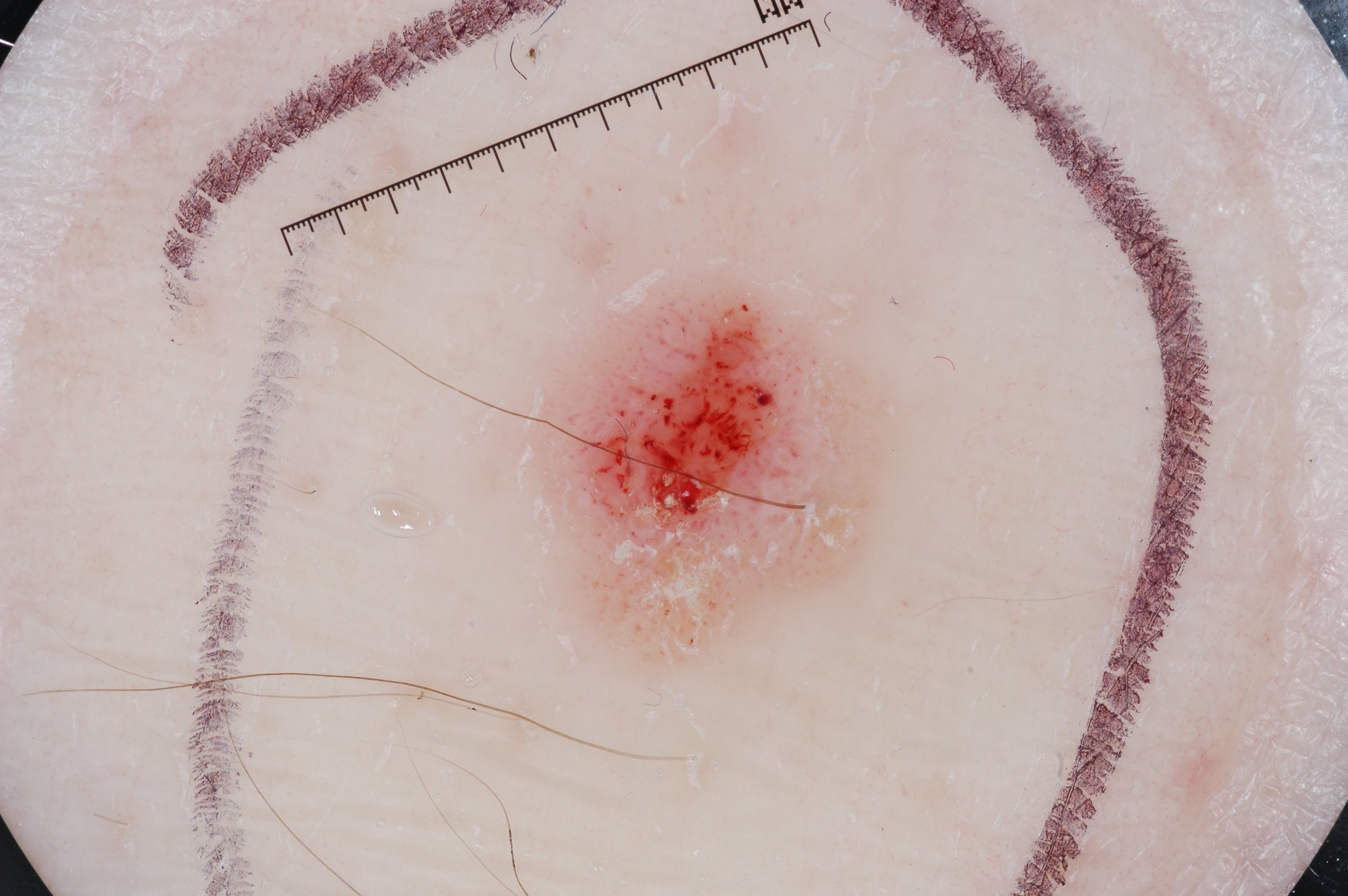Summary: The subject is a male aged approximately 60. A dermoscopy image of a single skin lesion. In (x1, y1, x2, y2) order, lesion location: [548, 287, 874, 658]. Dermoscopic review identifies no streaks, pigment network, milia-like cysts, or negative network. Impression: Clinically diagnosed as a seborrheic keratosis, a benign lesion.